A female subject, roughly 30 years of age; a dermoscopic close-up of a skin lesion — 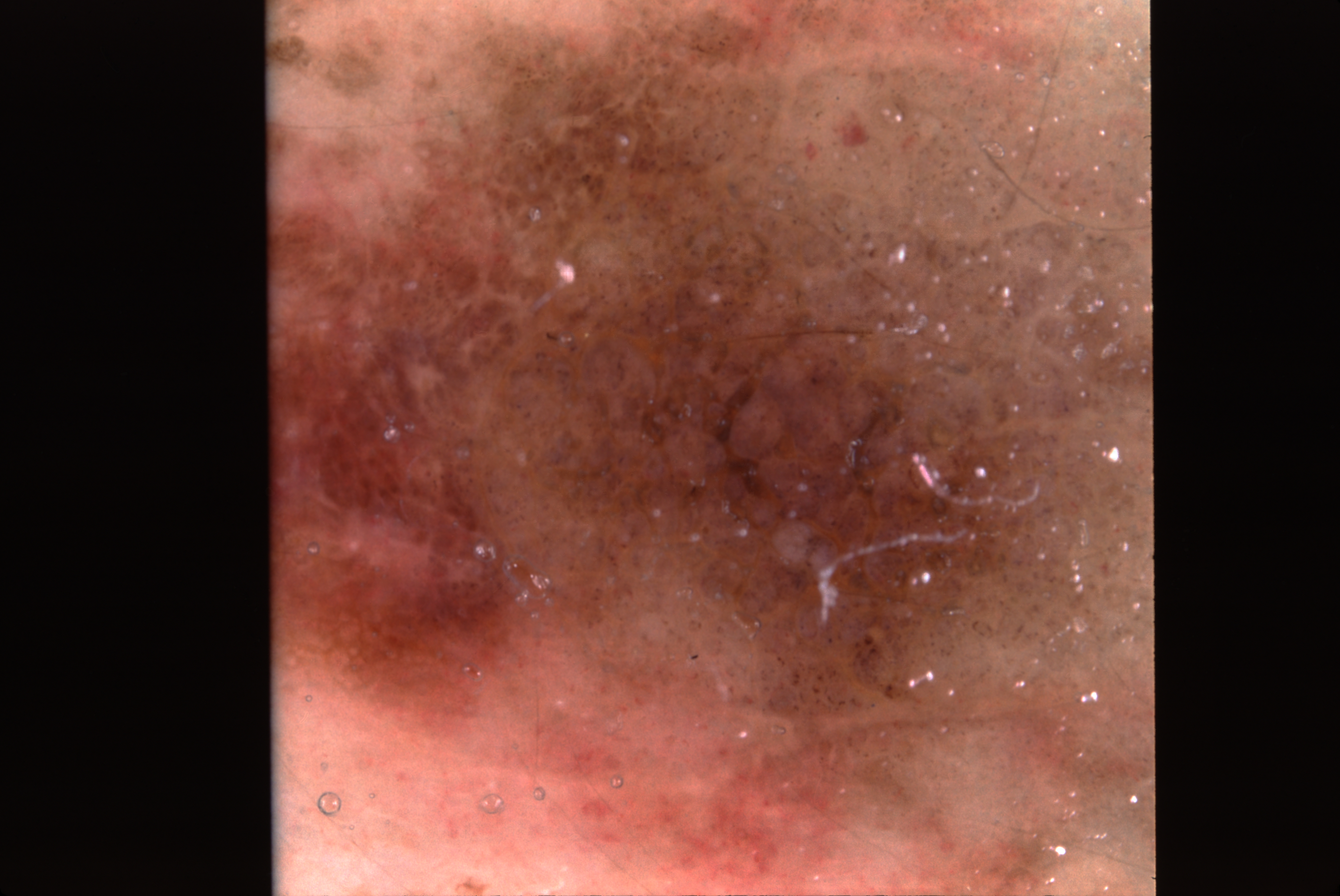Findings: The lesion is clipped by the edge of the image. Dermoscopy demonstrates pigment network and negative network. With coordinates (x1, y1, x2, y2), the lesion occupies the region [269, 0, 1156, 895]. The lesion takes up a large portion of the image. Conclusion: The diagnostic assessment was a melanocytic nevus, a benign lesion.